Dermoscopy of a skin lesion. The patient describes having few moles overall. A male patient 78 years of age. Imaged for a research study, with no referral diagnosis recorded. The patient reports a personal history of cancer. The patient says their skin reddens with sun exposure: 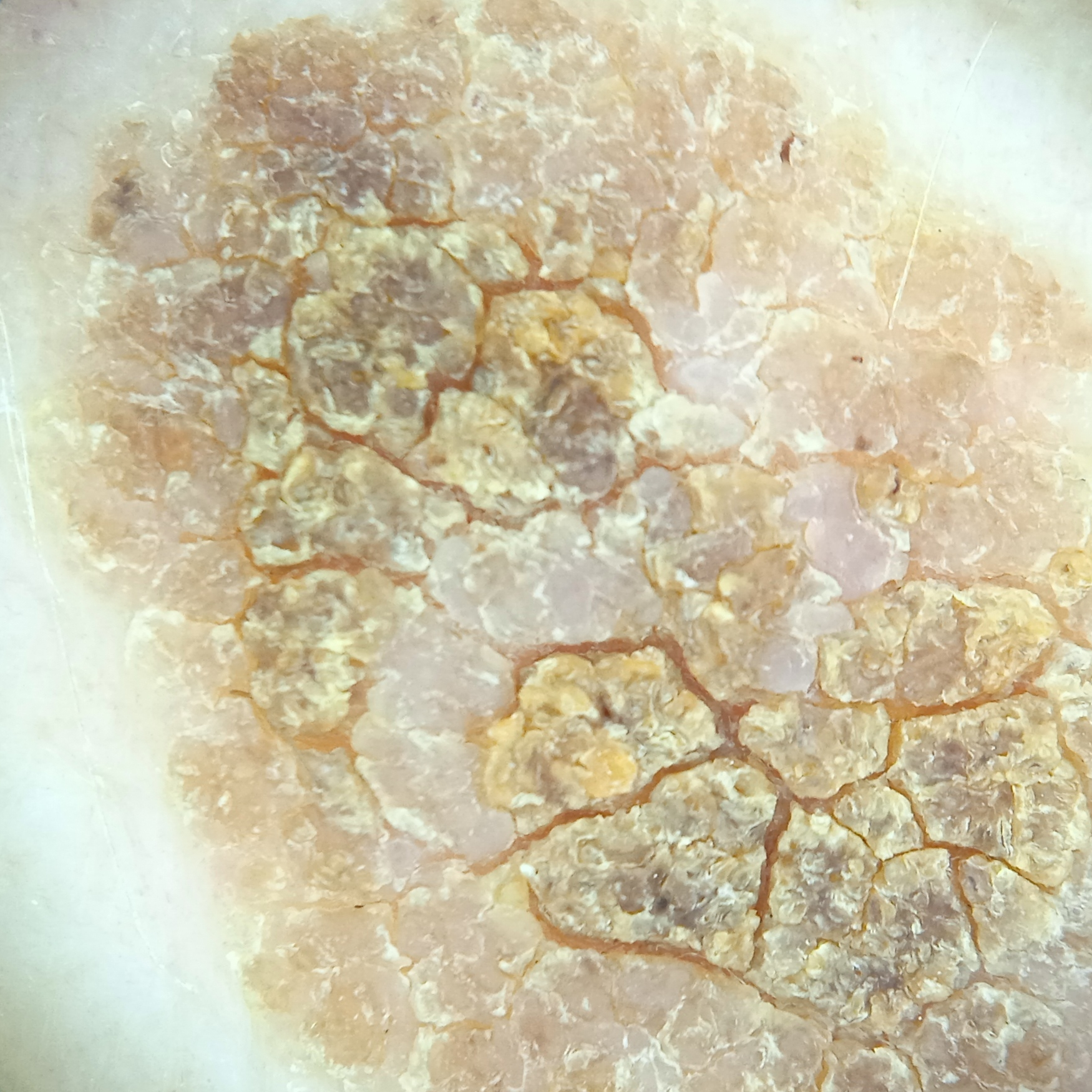- anatomic site — the back
- diameter — 15.1 mm
- assessment — seborrheic keratosis (dermatologist consensus)